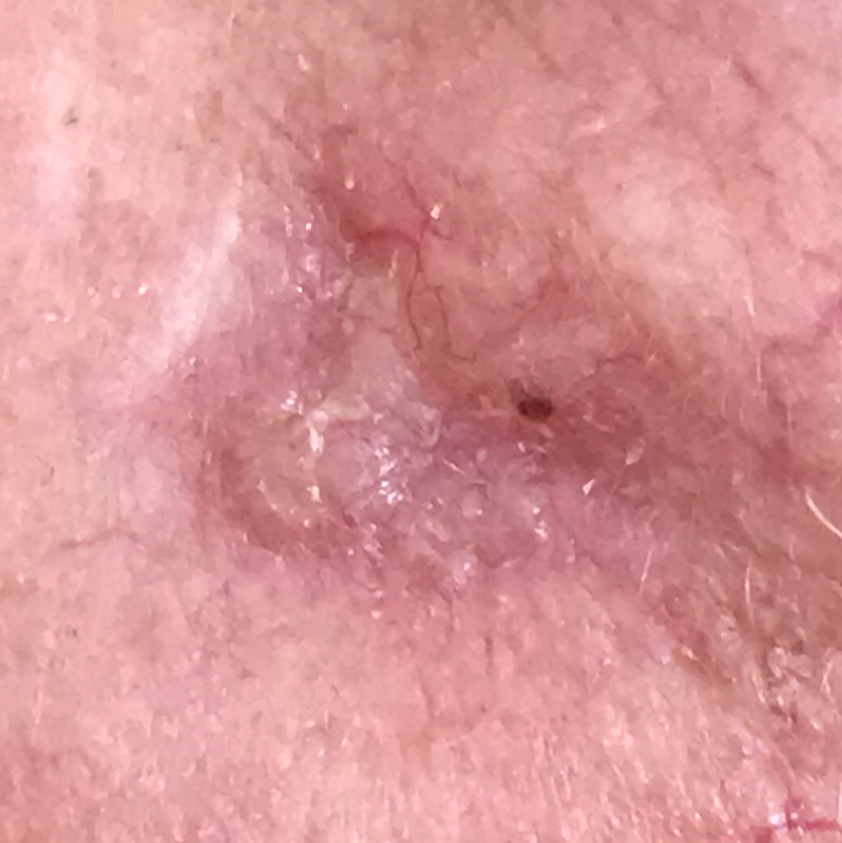anatomic site: the face; symptoms: elevation / no bleeding, no change in appearance; diagnosis: basal cell carcinoma (biopsy-proven).